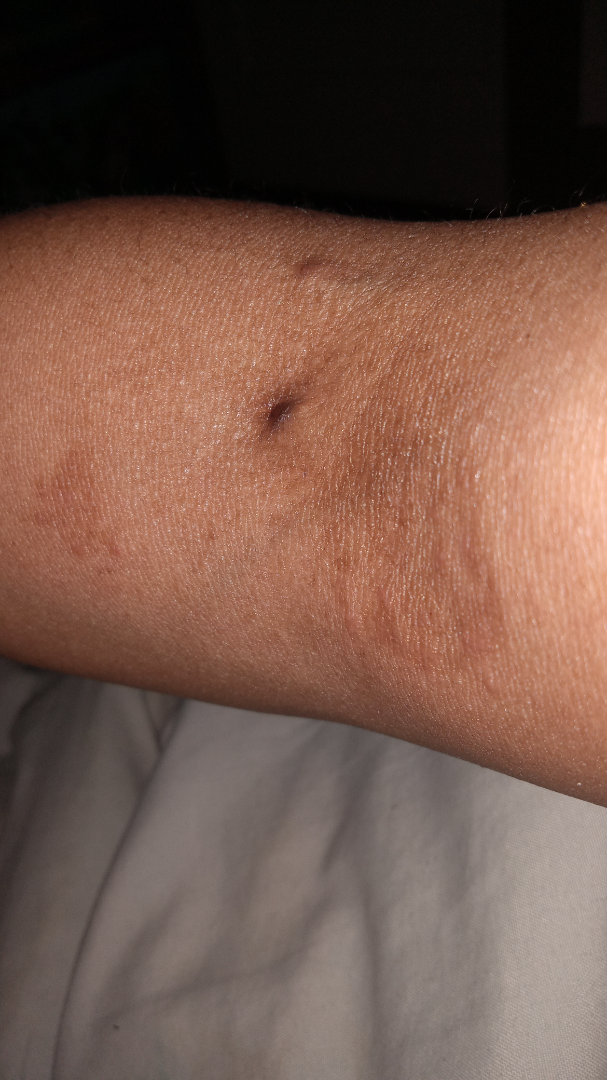<dermatology_case>
<shot_type>at an angle</shot_type>
<patient>female, age 50–59</patient>
<texture>raised or bumpy</texture>
</dermatology_case>